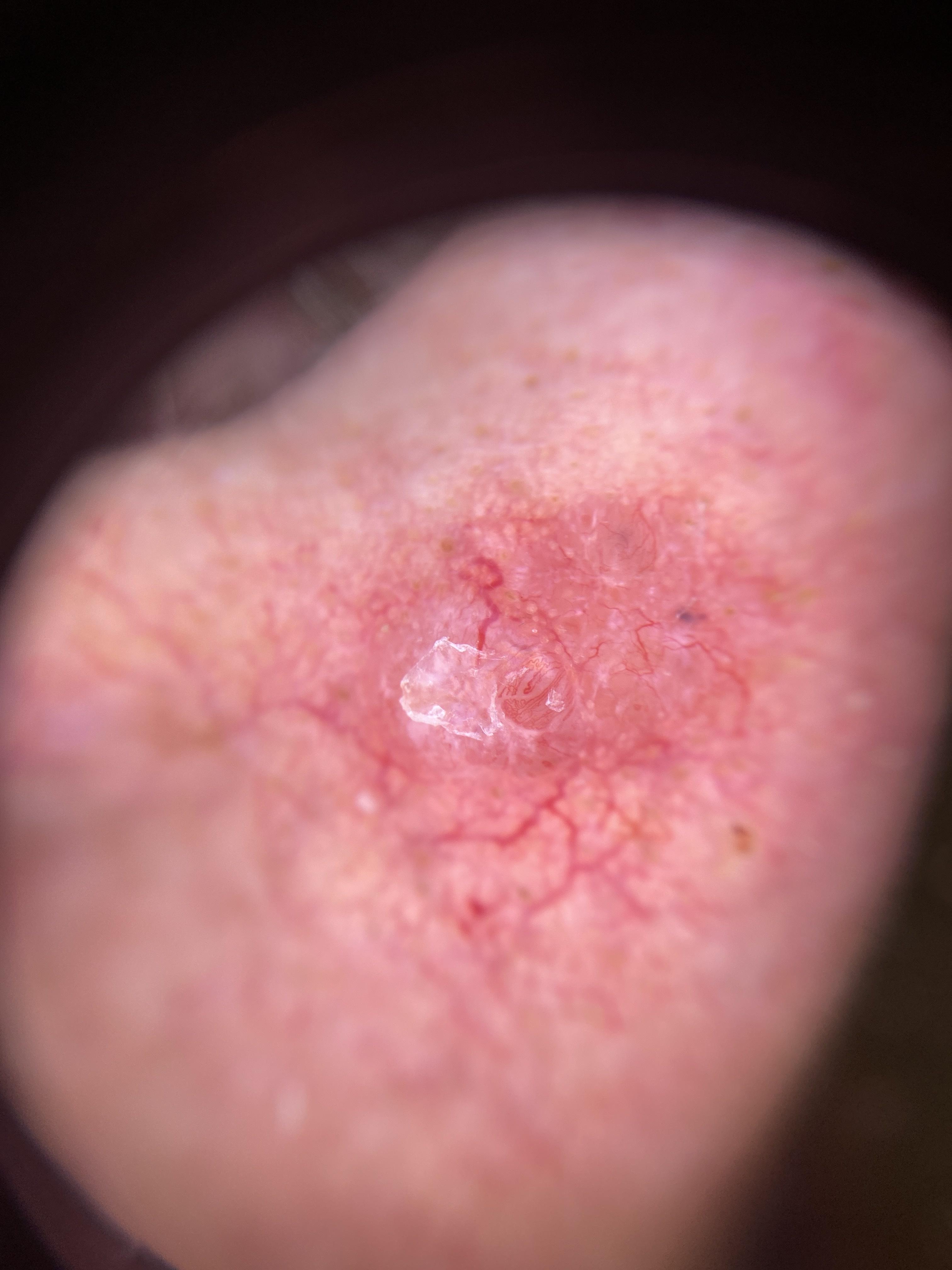Summary:
A skin lesion imaged with contact-polarized dermoscopy. The patient is FST II. The lesion was found on the head or neck.
Diagnosis:
Confirmed on histopathology as a skin cancer — a basal cell carcinoma.